The lesion involves the head or neck, the photograph is a close-up of the affected area:
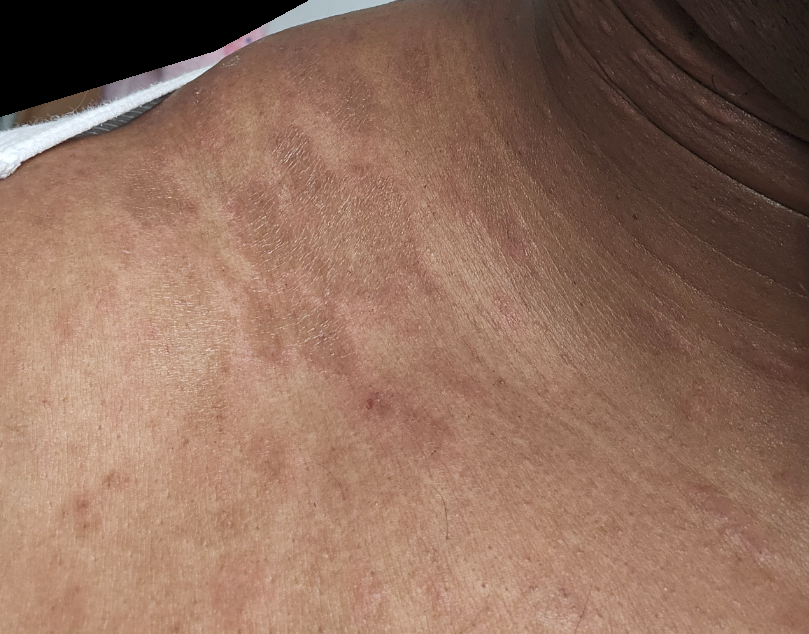assessment: ungradable on photographic review.